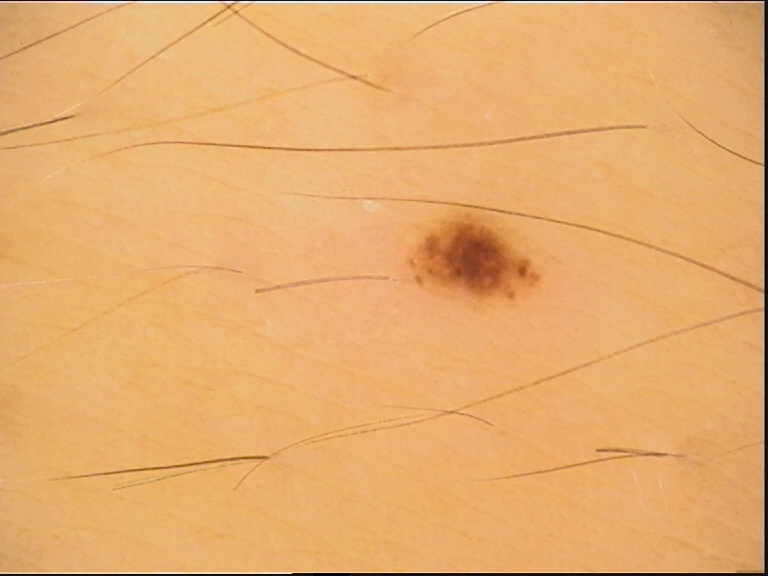A dermoscopic photograph of a skin lesion.
Diagnosed as a benign lesion — a dysplastic junctional nevus.